A dermoscopic close-up of a skin lesion:
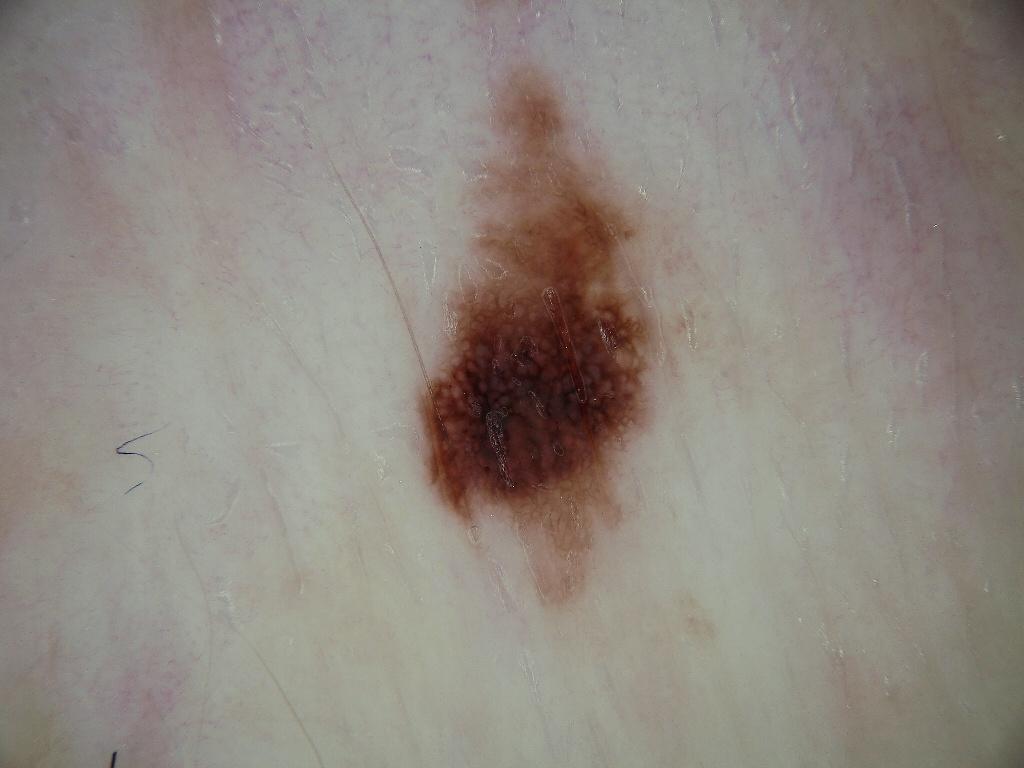The lesion's extent is <box>412, 56, 688, 609</box>. Expert review diagnosed this as a melanocytic nevus.